A skin lesion imaged with a dermatoscope.
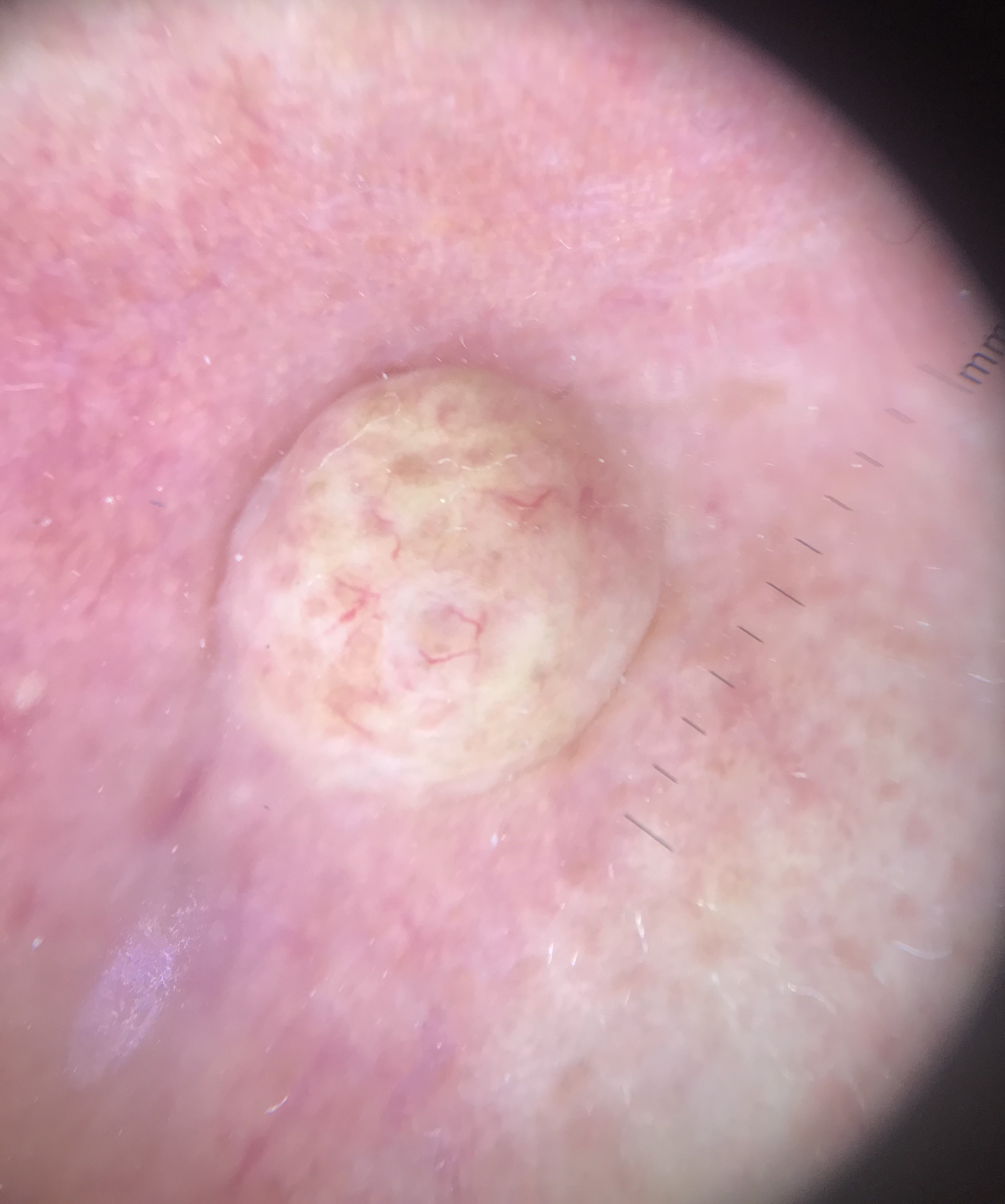class — dermal nevus (expert consensus).